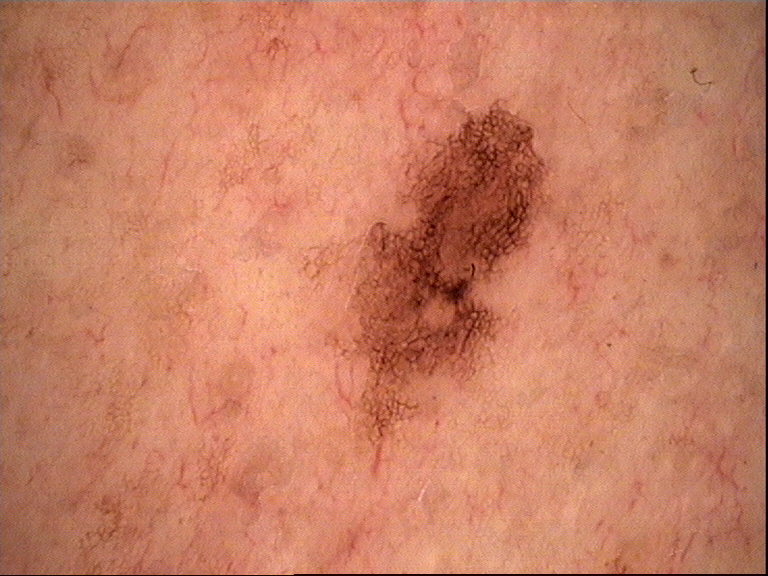Diagnosed as a dysplastic junctional nevus.